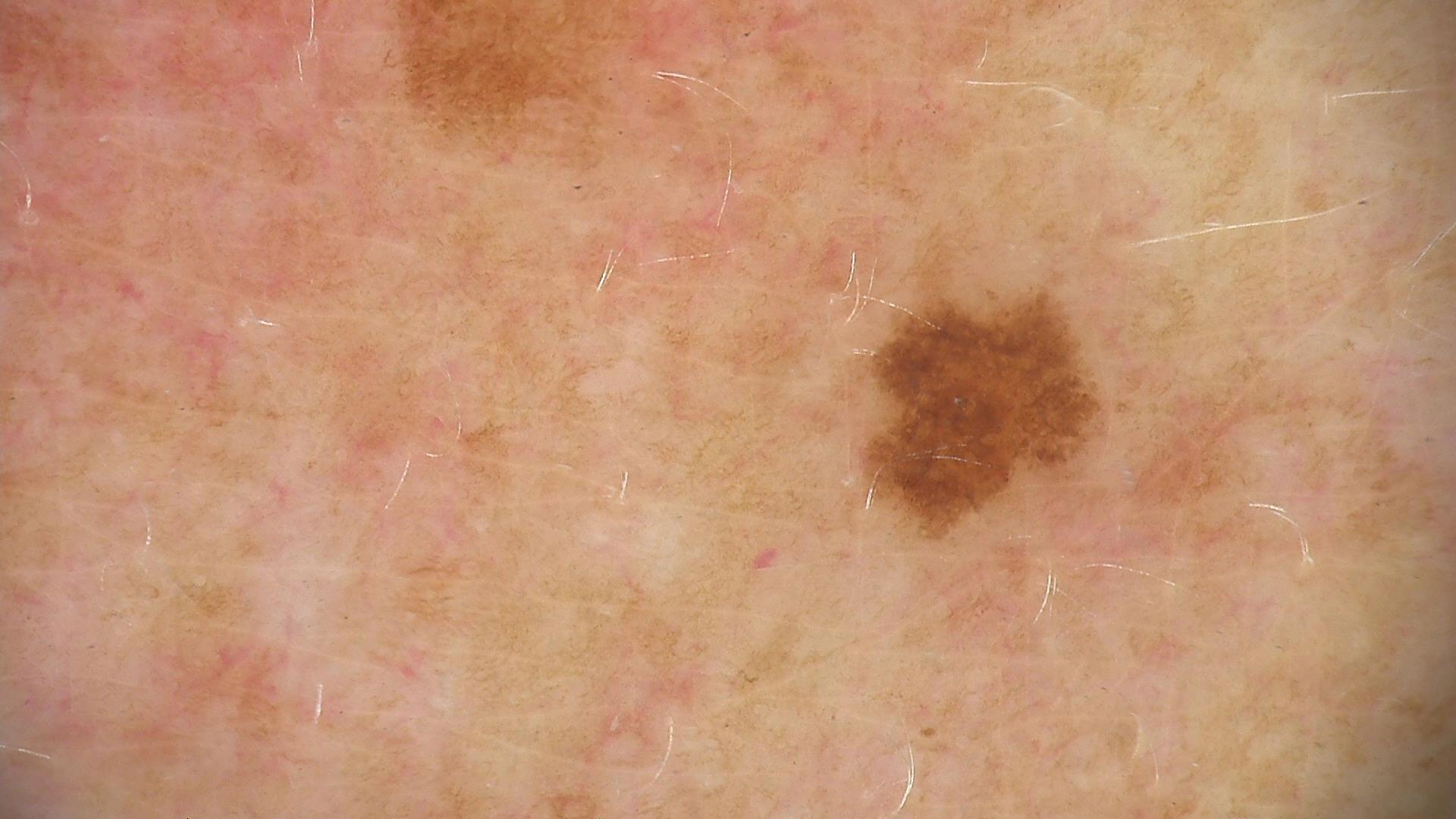Case:
A dermoscopic photograph of a skin lesion.
Impression:
Consistent with a dysplastic junctional nevus.